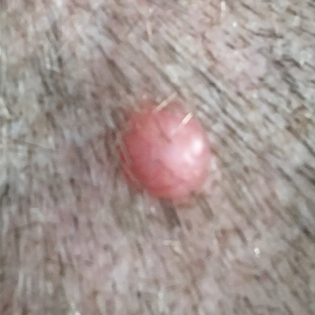Recorded as skin type II.
By history, alcohol use, no tobacco use, and no prior malignancy (patient or family).
A female subject age 76.
A clinical photograph of a skin lesion.
The lesion involves the face.
Measuring about 7 × 6 mm.
The patient reports that the lesion has grown and is elevated, but does not itch.
The biopsy diagnosis was a basal cell carcinoma.